A dermoscopic image of a skin lesion.
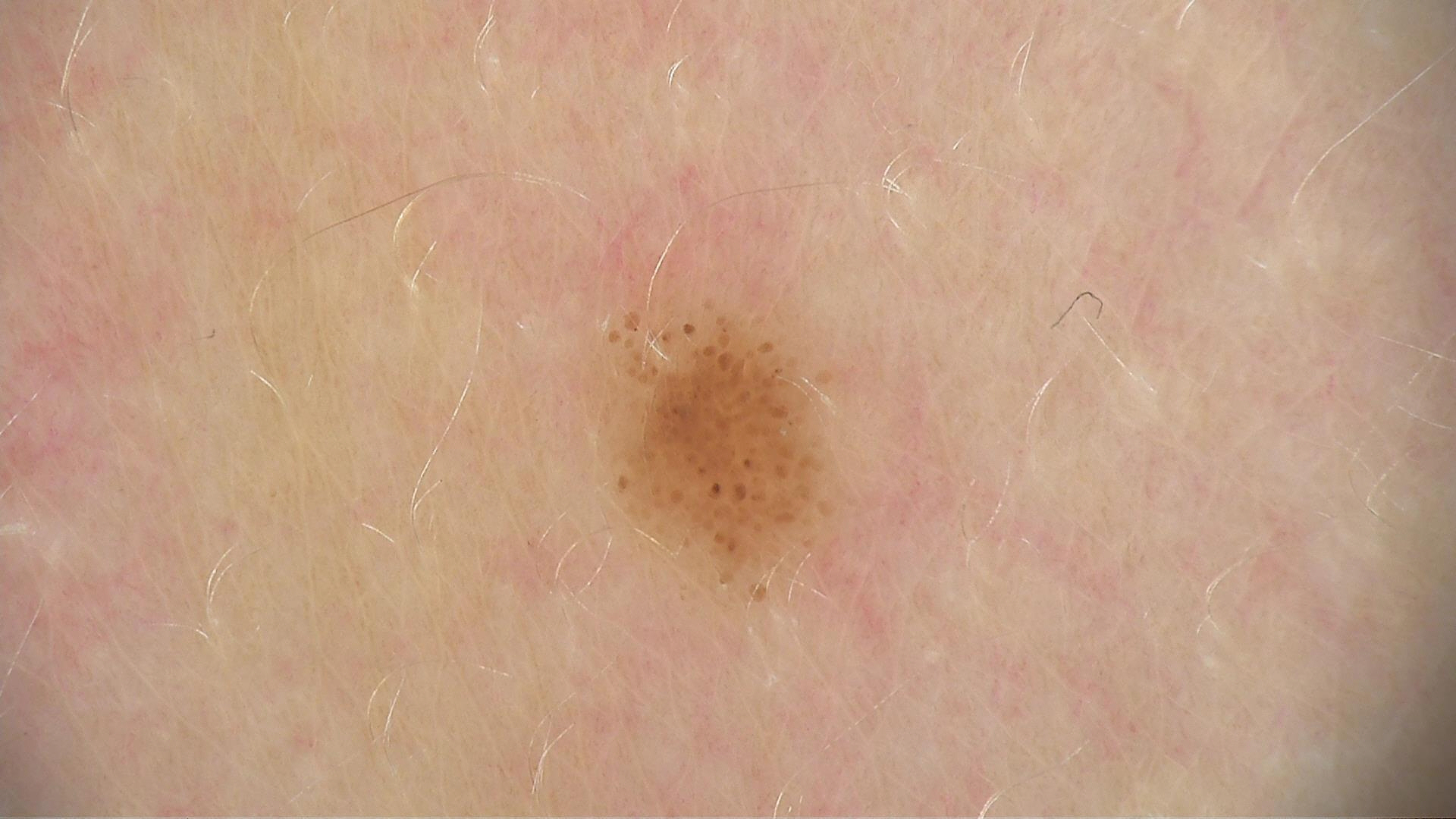diagnosis:
  name: dysplastic junctional nevus
  code: jd
  malignancy: benign
  super_class: melanocytic
  confirmation: expert consensus